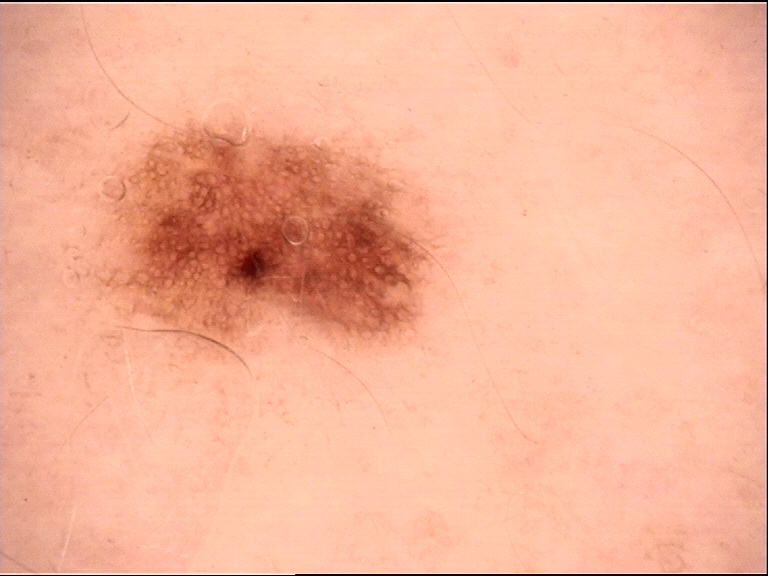Labeled as a dysplastic junctional nevus.